Located on the palm, arm, back of the hand and top or side of the foot; a close-up photograph:
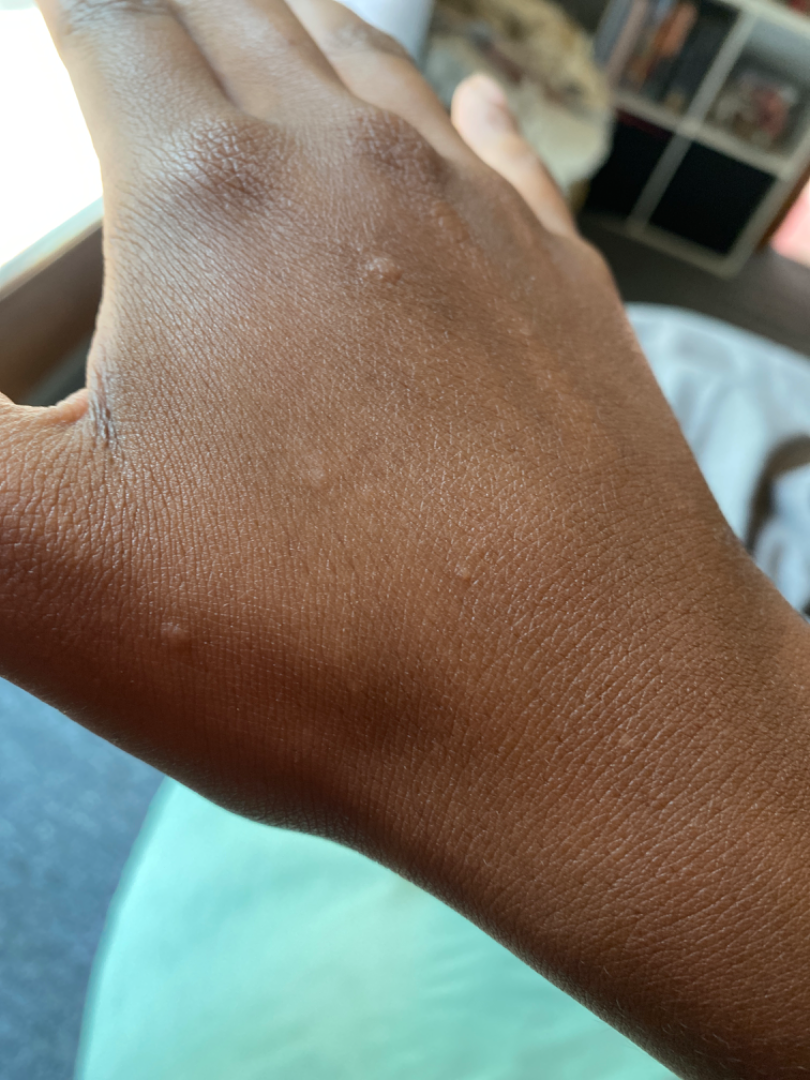Q: Could the case be diagnosed?
A: unable to determine
Q: Duration?
A: one to four weeks
Q: Texture?
A: raised or bumpy and fluid-filled